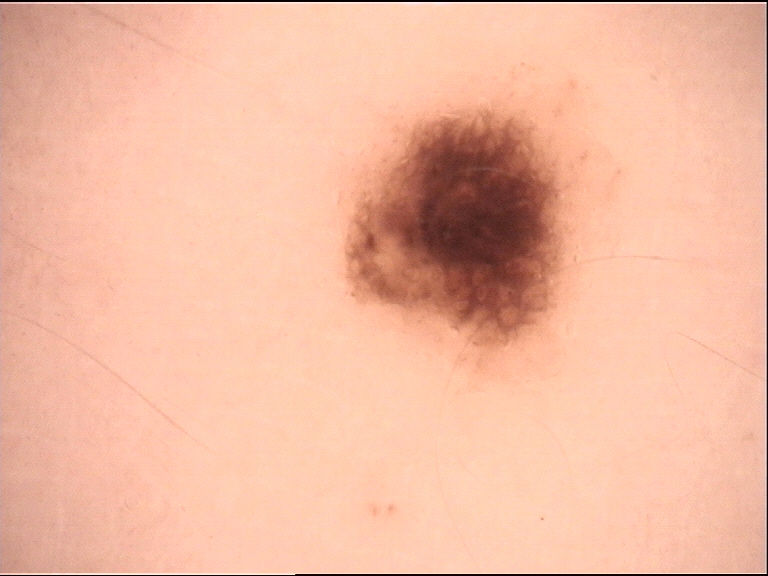Conclusion: Diagnosed as a benign lesion — a dysplastic junctional nevus.